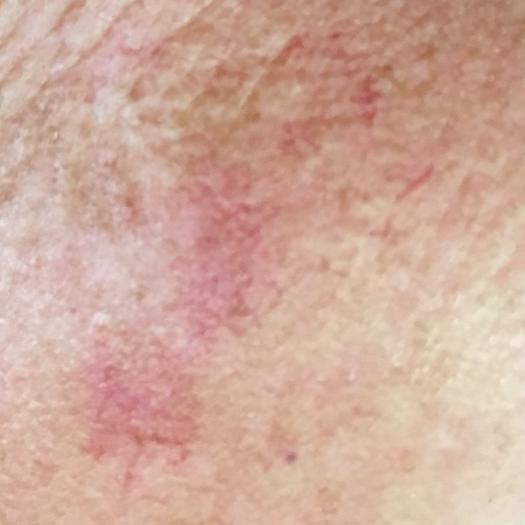A clinical photograph showing a skin lesion. A subject 63 years of age. The lesion is located on the face. The patient reports that the lesion itches, but does not hurt and has not grown. The consensus clinical diagnosis was an actinic keratosis.